A dermoscopic image of a skin lesion:
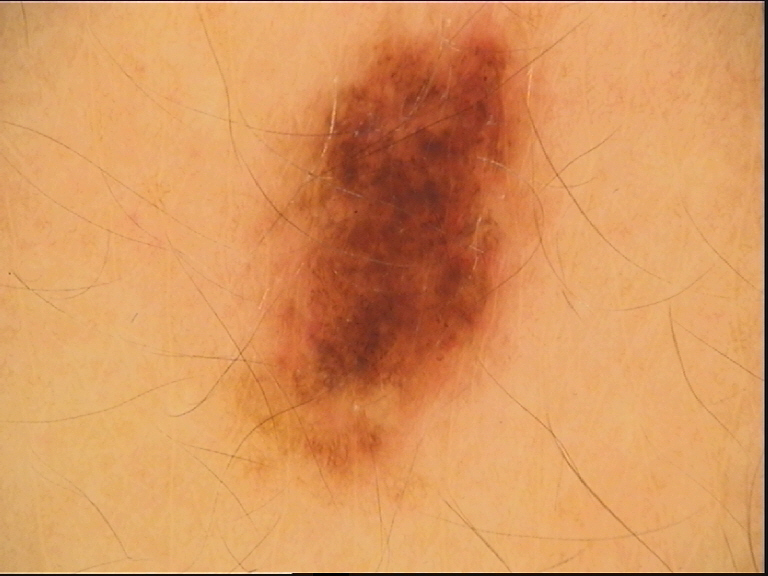Q: What was the diagnostic impression?
A: dysplastic junctional nevus (expert consensus)